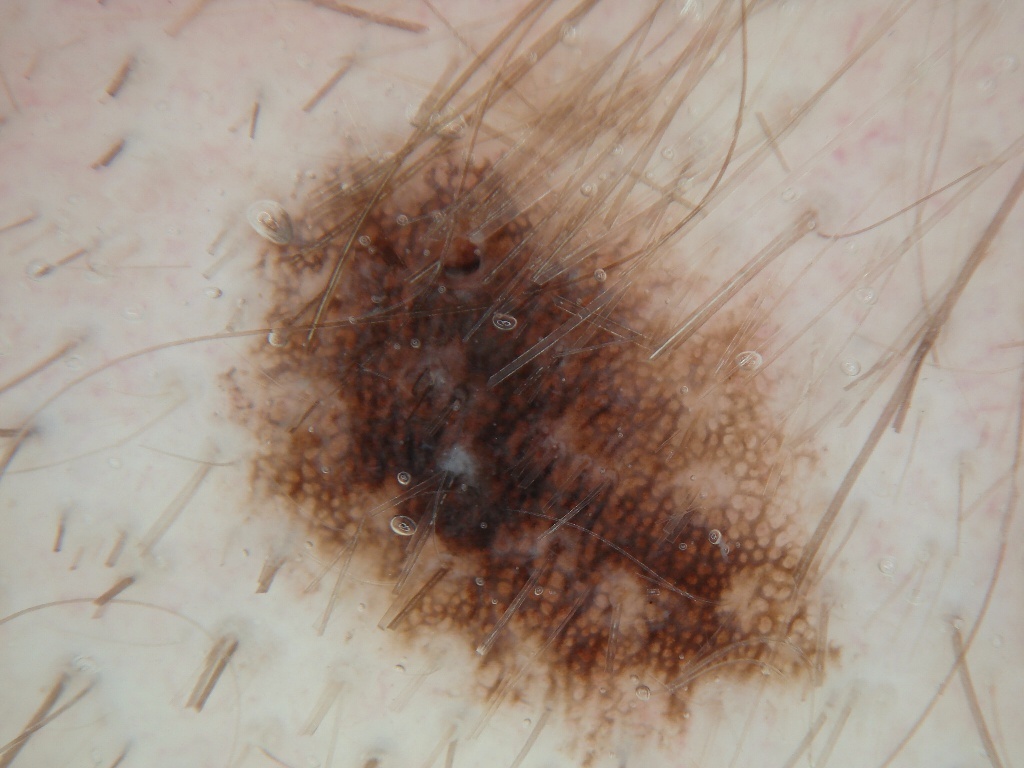Image and clinical context:
A dermatoscopic image of a skin lesion. A male subject, aged 23-27. The lesion occupies the region left=202, top=16, right=886, bottom=766. The dermoscopic pattern shows pigment network; no milia-like cysts, globules, streaks, or negative network. The lesion covers approximately 47% of the dermoscopic field.
Impression:
The diagnostic assessment was a melanocytic nevus.